A dermoscopic close-up of a skin lesion.
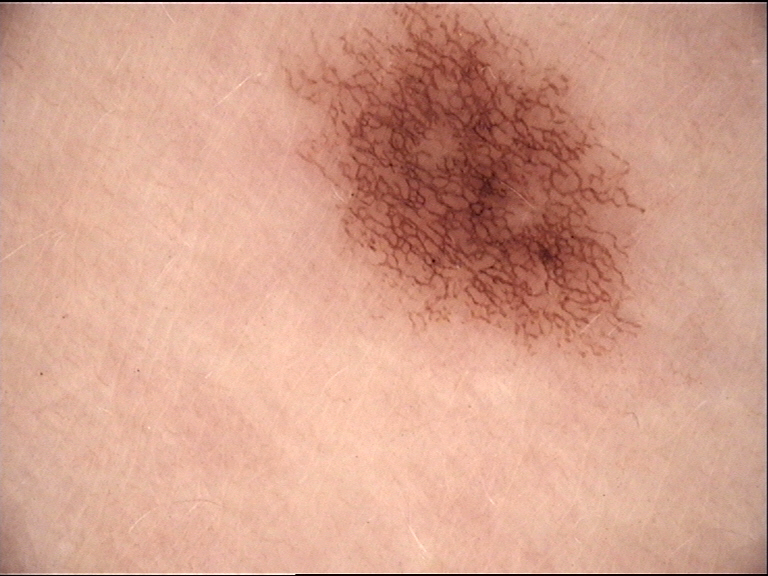lesion type = banal | diagnosis = junctional nevus (expert consensus).